A dermoscopic image of a skin lesion.
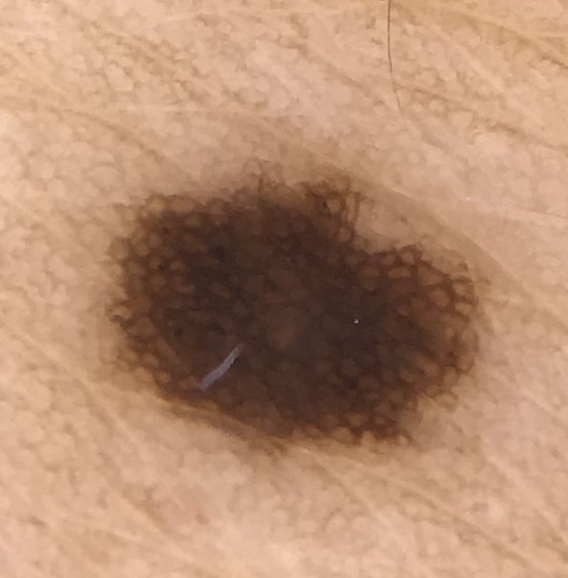The morphology is that of a banal lesion. Labeled as a junctional nevus.